An image taken at an angle; the affected area is the leg; female patient, age 30–39 — 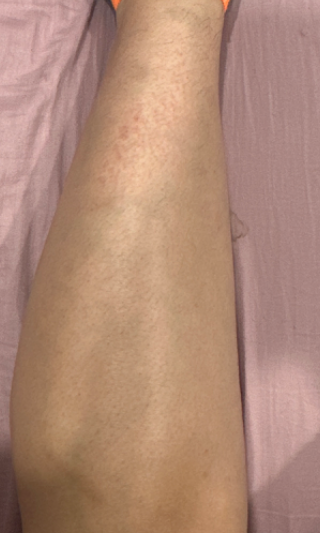Findings: The case was indeterminate on photographic review.